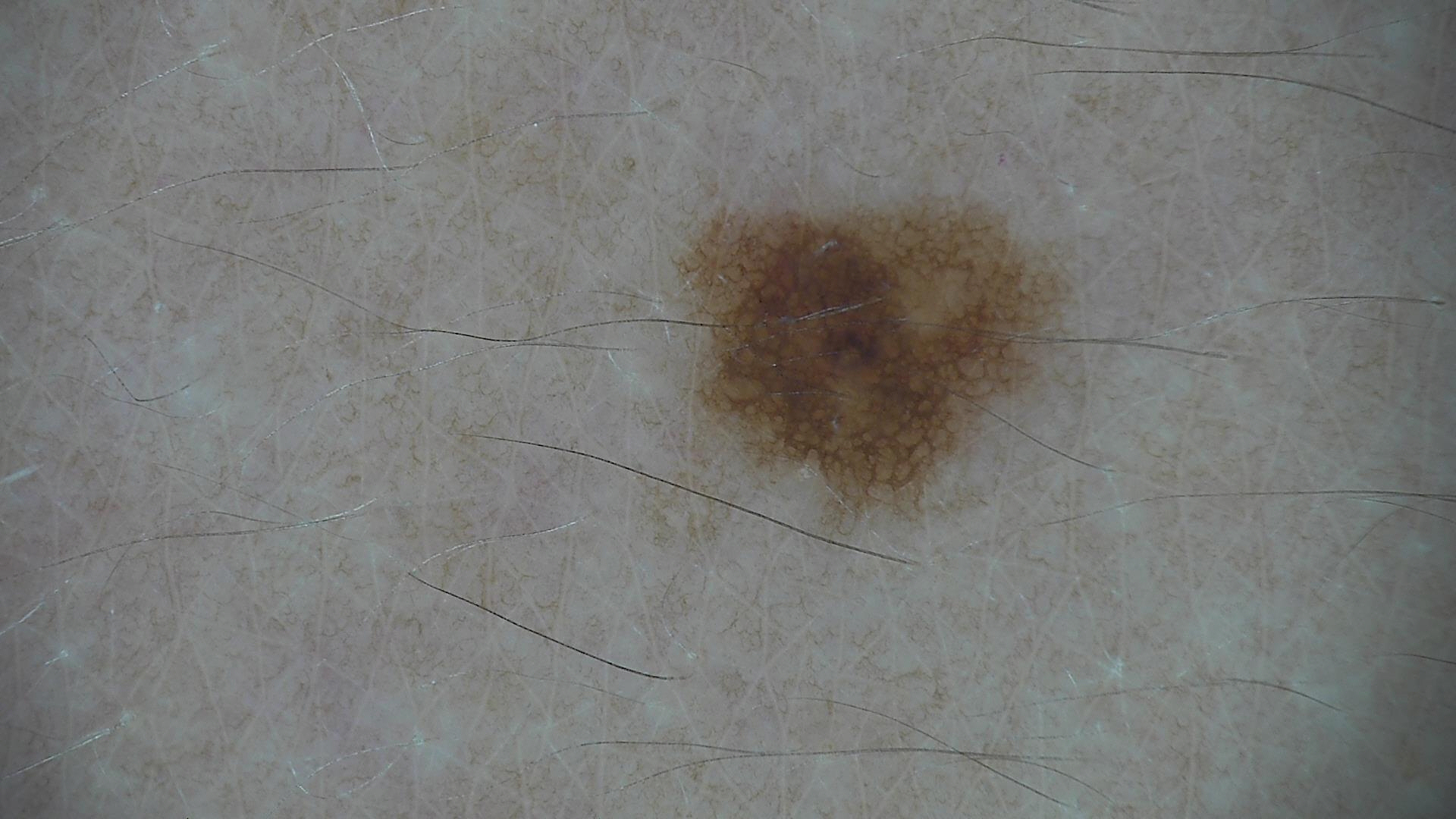modality: dermatoscopy; assessment: dysplastic junctional nevus (expert consensus).